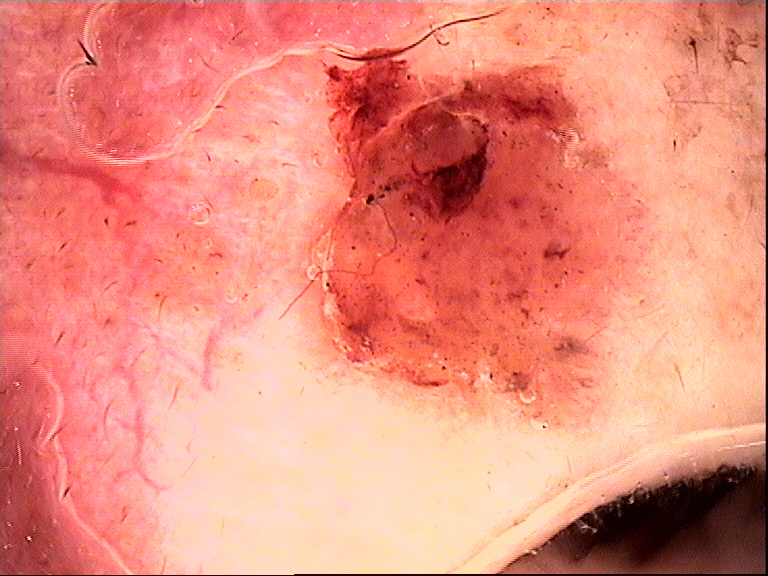* label: squamous cell carcinoma (biopsy-proven)